The patient indicates the lesion is raised or bumpy. The photograph is a close-up of the affected area. Symptoms reported: bothersome appearance and enlargement. The condition has been present for one to four weeks.
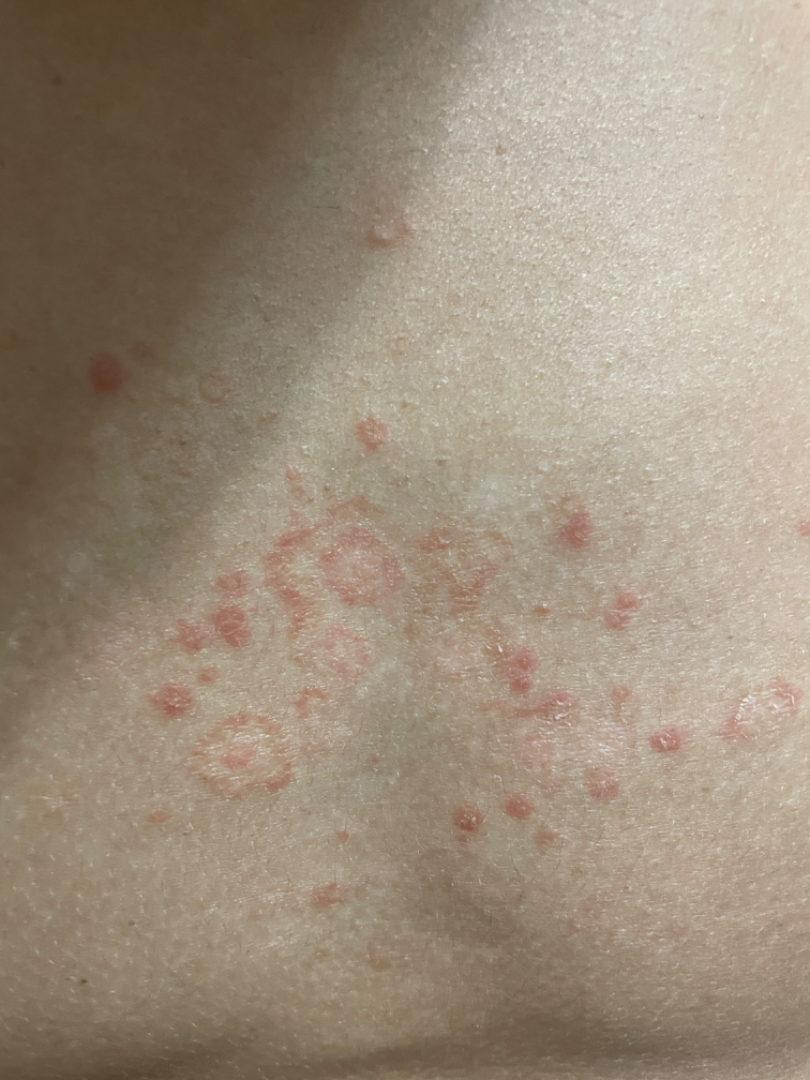Review: Single-reviewer assessment: Erythema gyratum repens, Seborrheic Dermatitis and Erythema marginatum in acute rheumatic fever were considered with similar weight.